A male subject in their 70s · the chart notes pesticide exposure · a clinical photograph of a skin lesion · the patient was assessed as FST II — 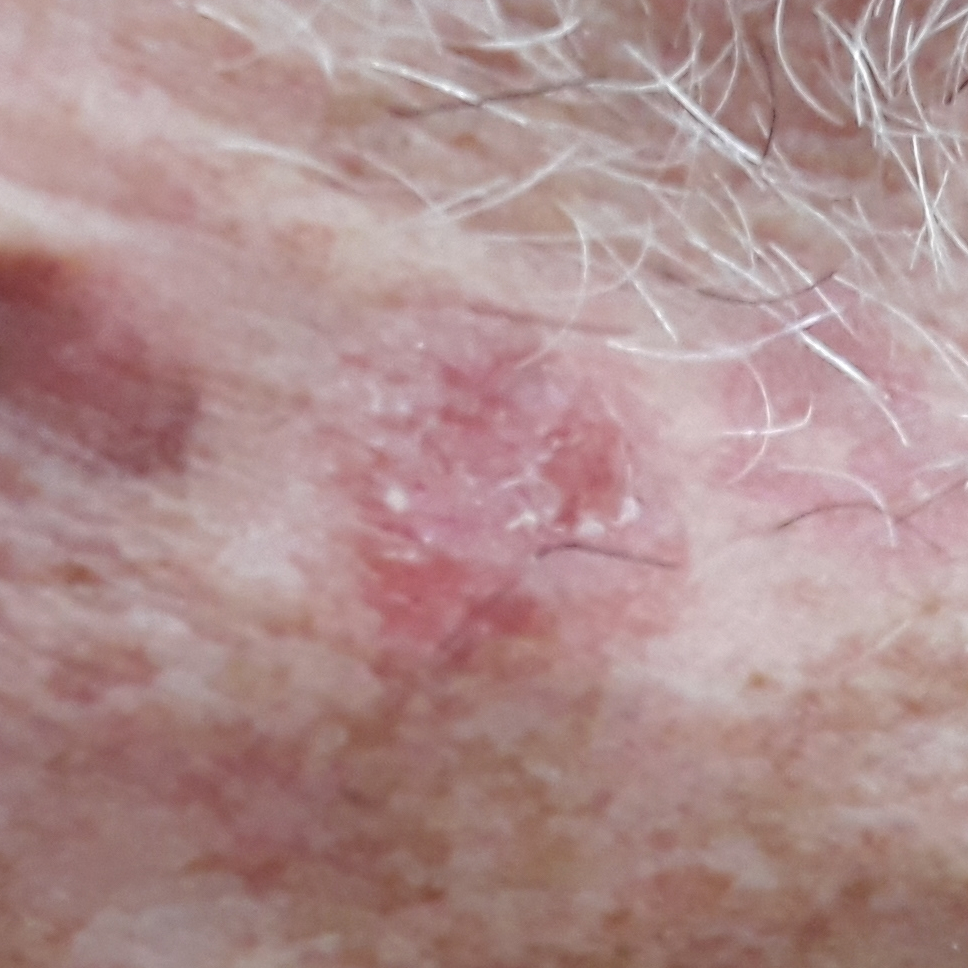body site: the face
diameter: approx. 10 × 10 mm
reported symptoms: change in appearance, growth, itching
diagnosis: squamous cell carcinoma (biopsy-proven)